A skin lesion imaged with a dermatoscope:
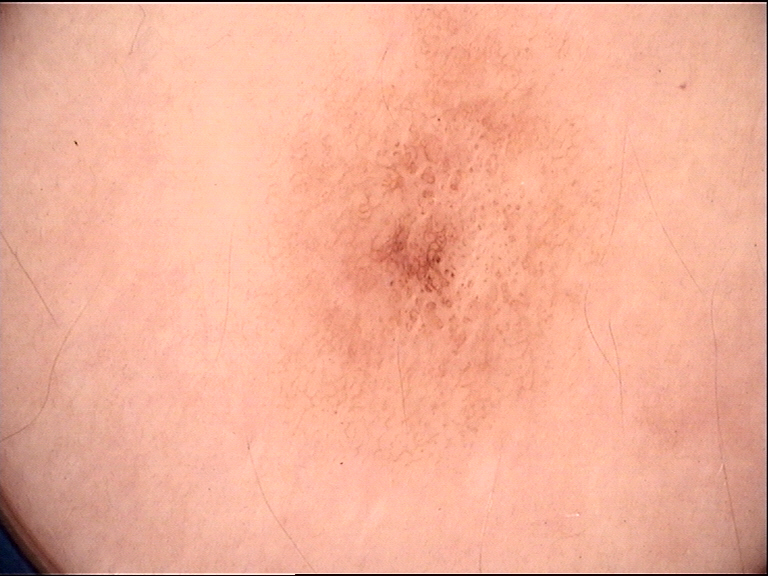Impression:
Consistent with a benign lesion — a dysplastic junctional nevus.